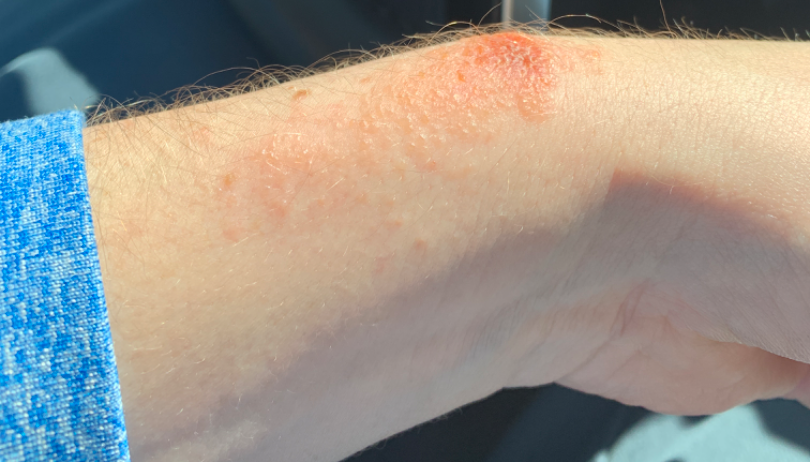reported symptoms — itching; patient describes the issue as — a rash; affected area — arm, top or side of the foot, front of the torso, leg and back of the hand; present for — less than one week; image framing — at an angle; described texture — raised or bumpy; skin tone — lay reviewers estimated Monk skin tone scale 2 or 3 (two reviewer pools); assessment — consistent with Allergic Contact Dermatitis.